The photograph was taken at an angle; the contributor notes bothersome appearance, enlargement, itching and darkening; Fitzpatrick phototype II; the contributor notes the lesion is rough or flaky and raised or bumpy; the contributor notes the condition has been present for one to four weeks; the patient considered this skin that appeared healthy to them; the leg is involved:
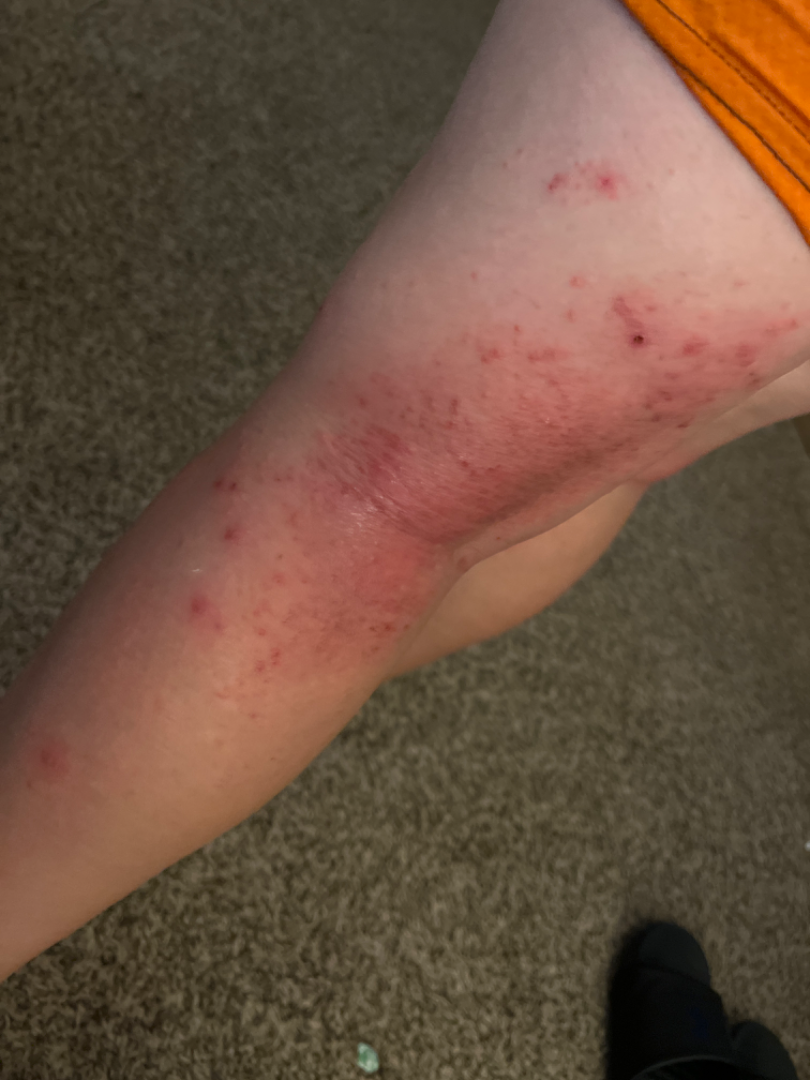The reviewing clinician's impression was: favoring Eczema.